This is a close-up image: 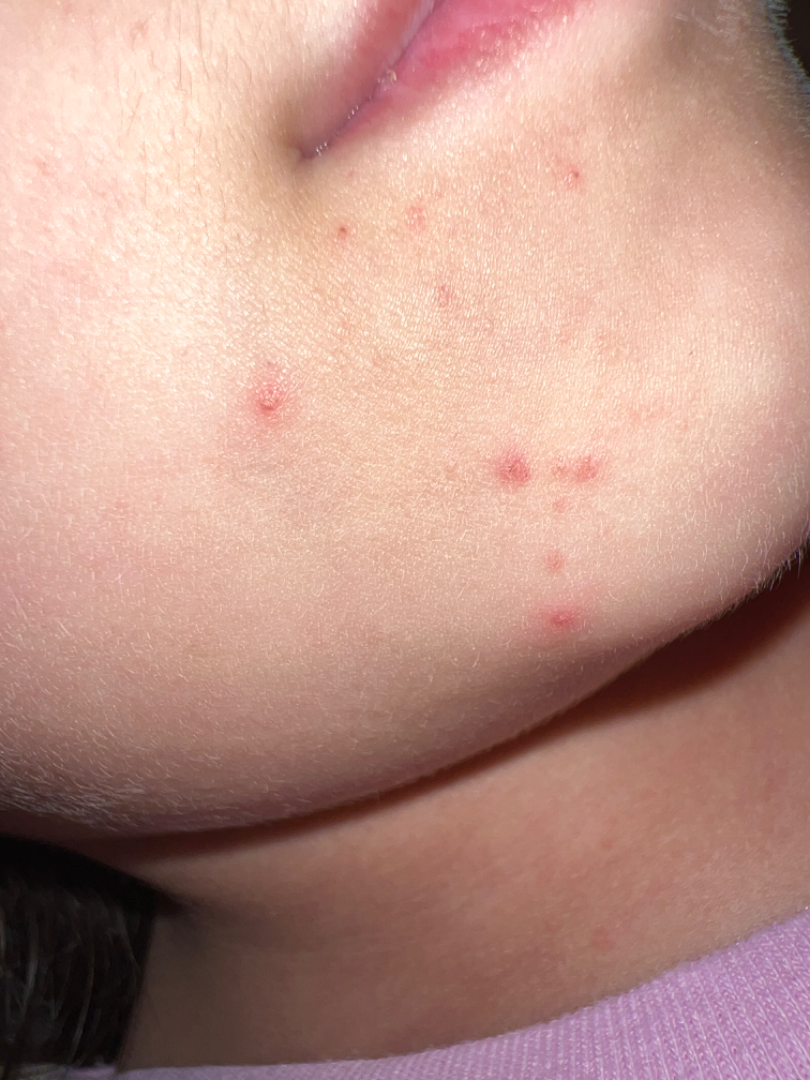{
  "differential": {
    "leading": [
      "Acne"
    ],
    "considered": [
      "Perioral Dermatitis"
    ]
  }
}